This is a dermoscopic photograph of a skin lesion · the patient is a male in their mid-20s: 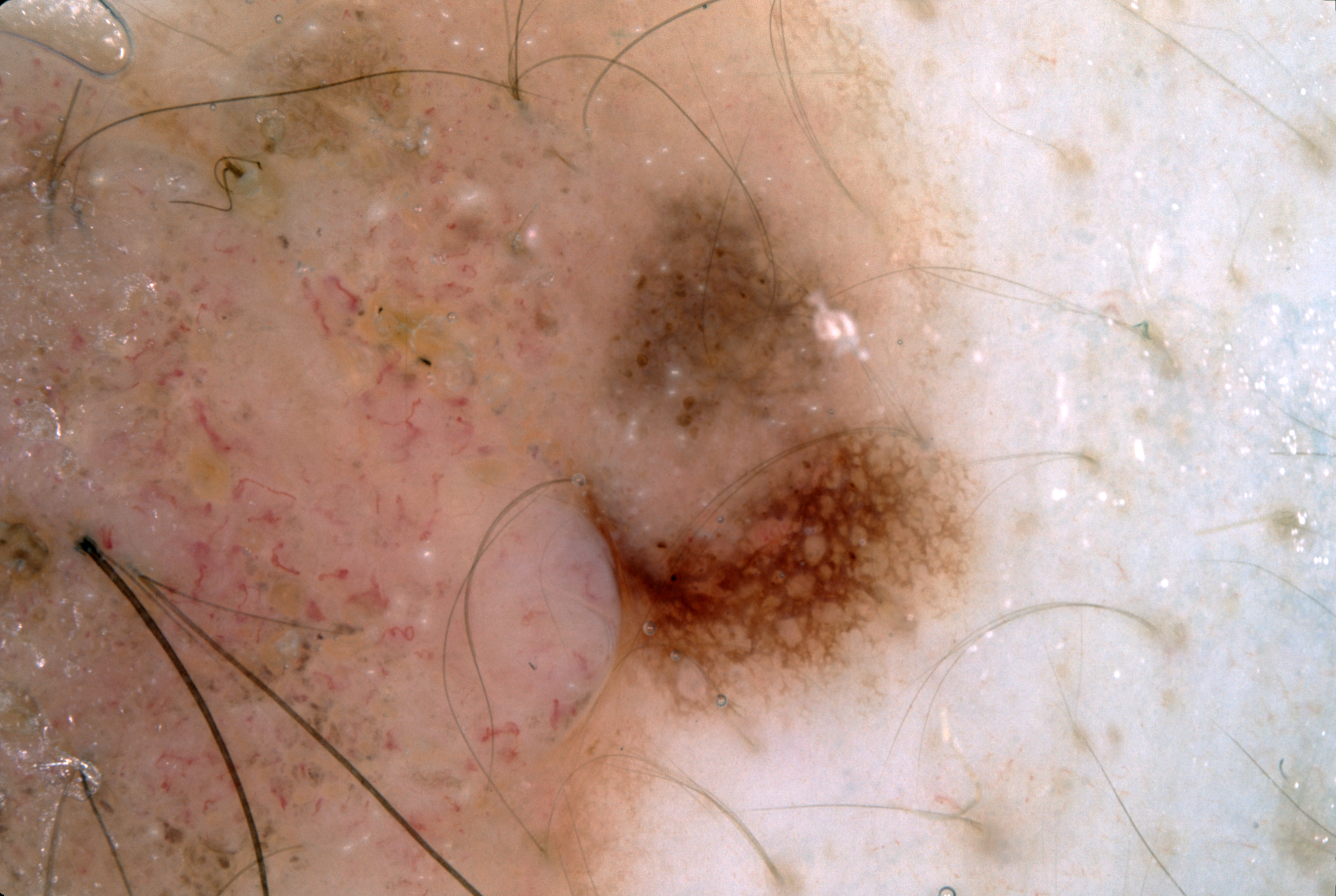Image and clinical context:
With coordinates (x1, y1, x2, y2), lesion location: 3/5/1026/893. The dermoscopic pattern shows pigment network. A large lesion occupying much of the field.
Impression:
The diagnostic assessment was a melanocytic nevus.